A dermatoscopic image of a skin lesion: 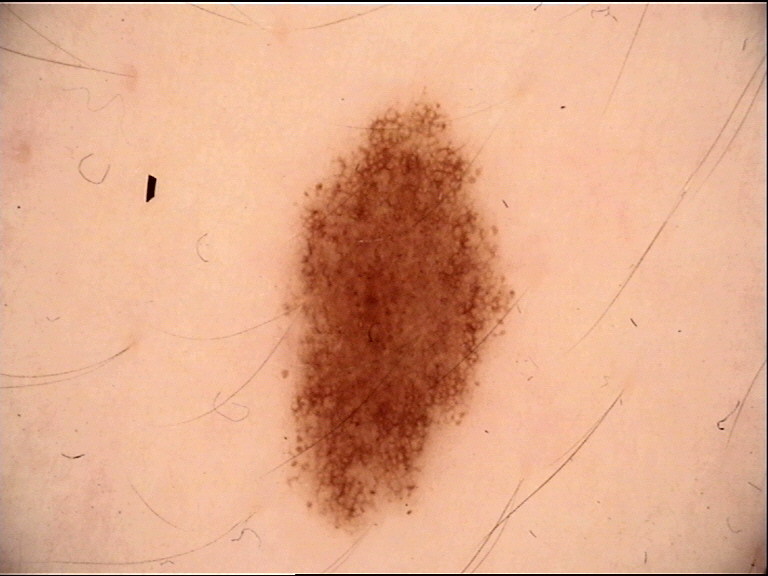Q: What is this lesion?
A: dysplastic junctional nevus (expert consensus)